This is a close-up image. The contributor notes itching, bothersome appearance, pain and burning. The lesion involves the arm. Texture is reported as raised or bumpy and fluid-filled. The patient described the issue as a rash. The contributor notes the condition has been present for less than one week — 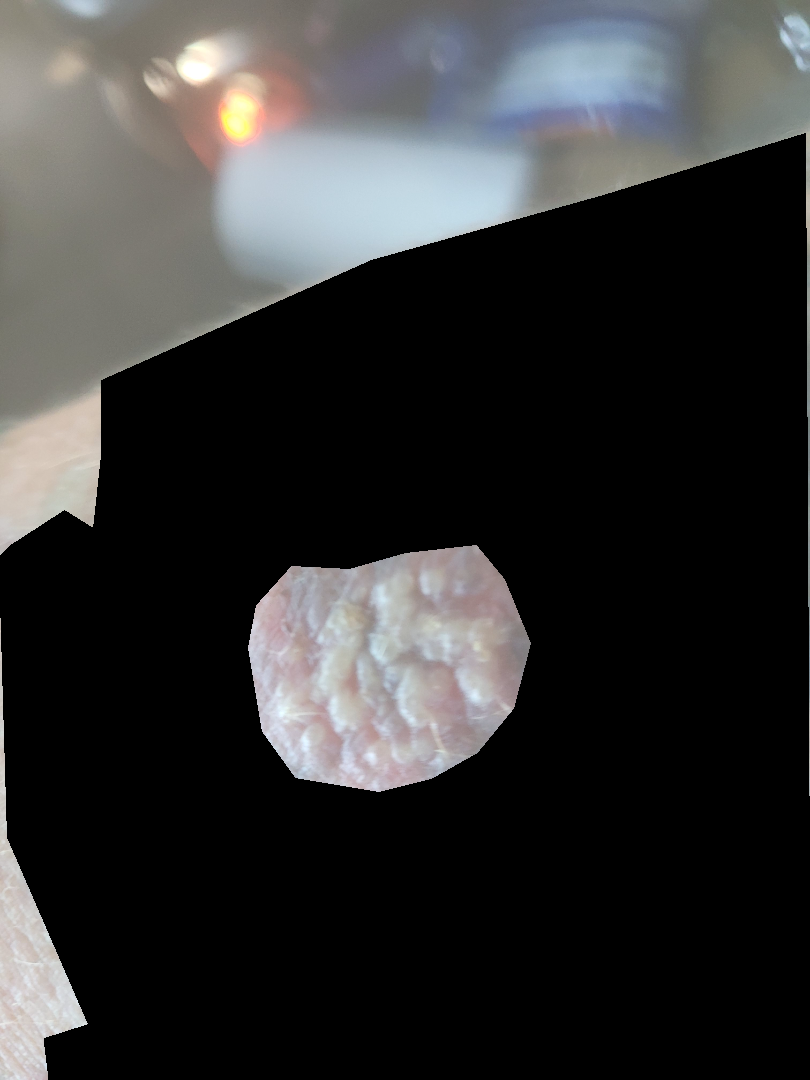Case summary:
* assessment · indeterminate